This image was taken at an angle. Present for one to four weeks. The patient also reports joint pain. The lesion involves the leg. The patient considered this a rash. Fitzpatrick skin type II; lay reviewers estimated MST 3 or 4 (two reviewer pools). Texture is reported as raised or bumpy and flat — 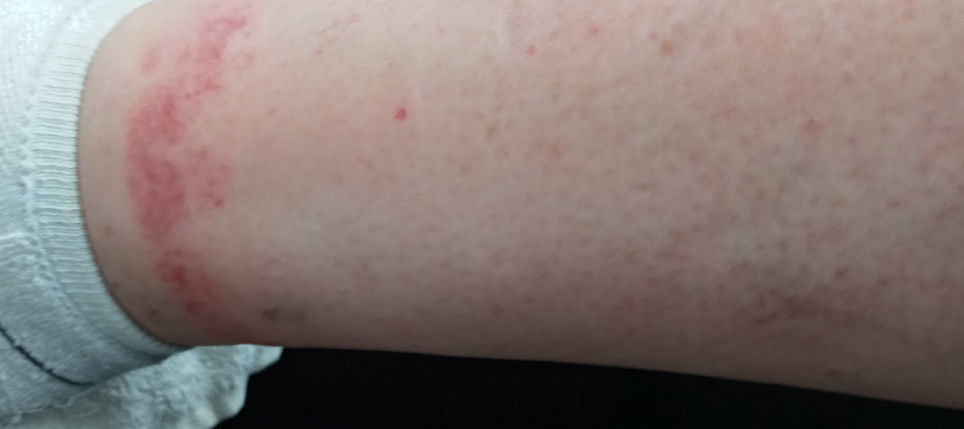Q: What is the differential diagnosis?
A: the impression was split between Contact dermatitis and Allergic Contact Dermatitis; less probable is Stasis Dermatitis; less likely is Acute dermatitis, NOS; a remote consideration is Pigmented purpuric eruption